This image was taken at an angle — 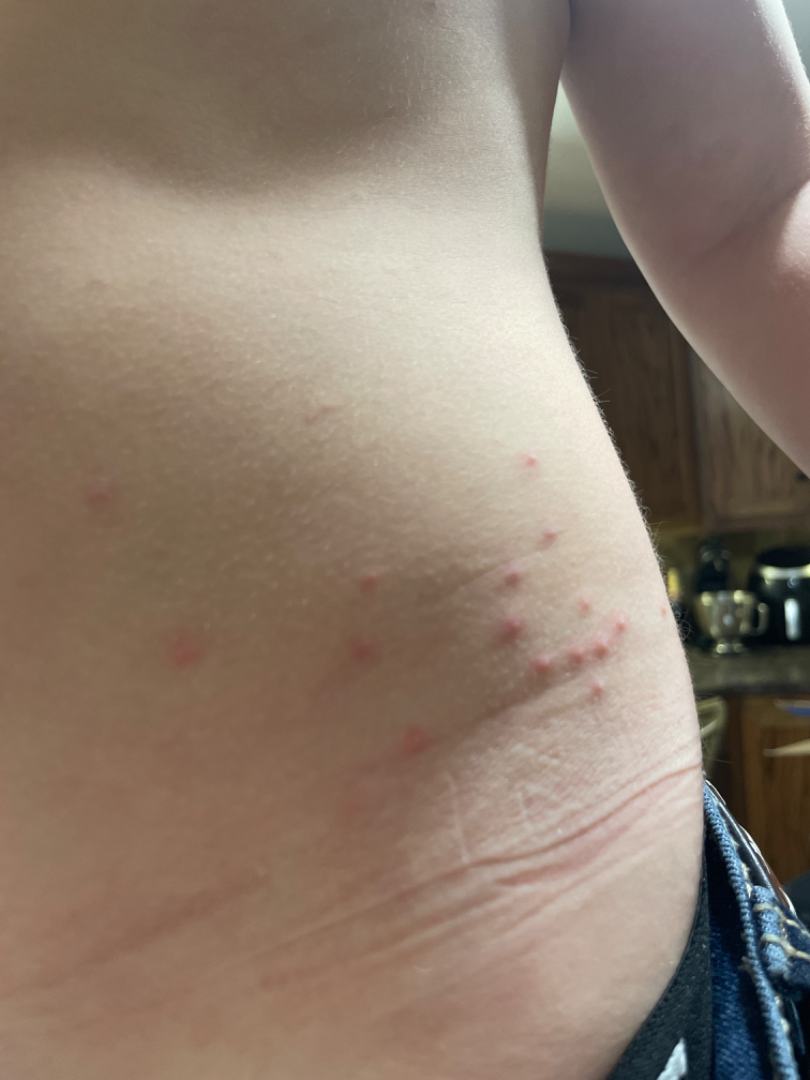Findings:
- differential diagnosis — favoring Folliculitis; also raised was Insect Bite